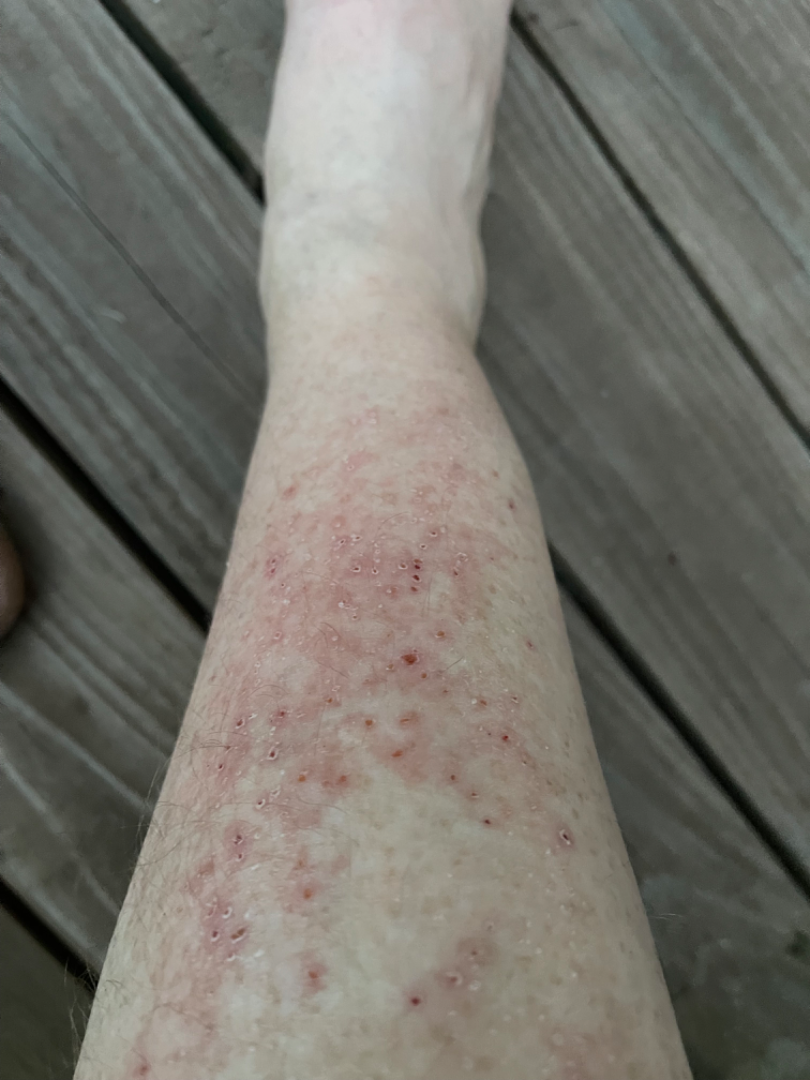A close-up photograph. On teledermatology review: the differential, in no particular order, includes Lichen Simplex Chronicus and Acute and chronic dermatitis.